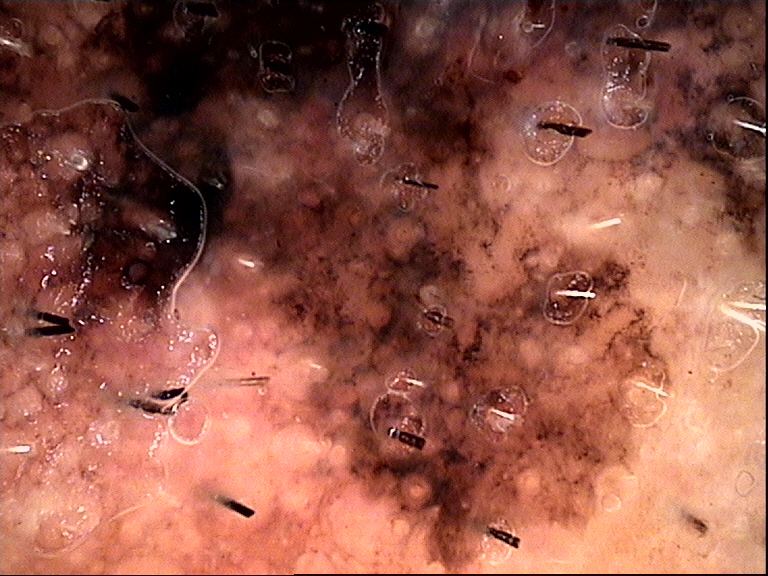image: dermoscopy | label: lentigo maligna (biopsy-proven).